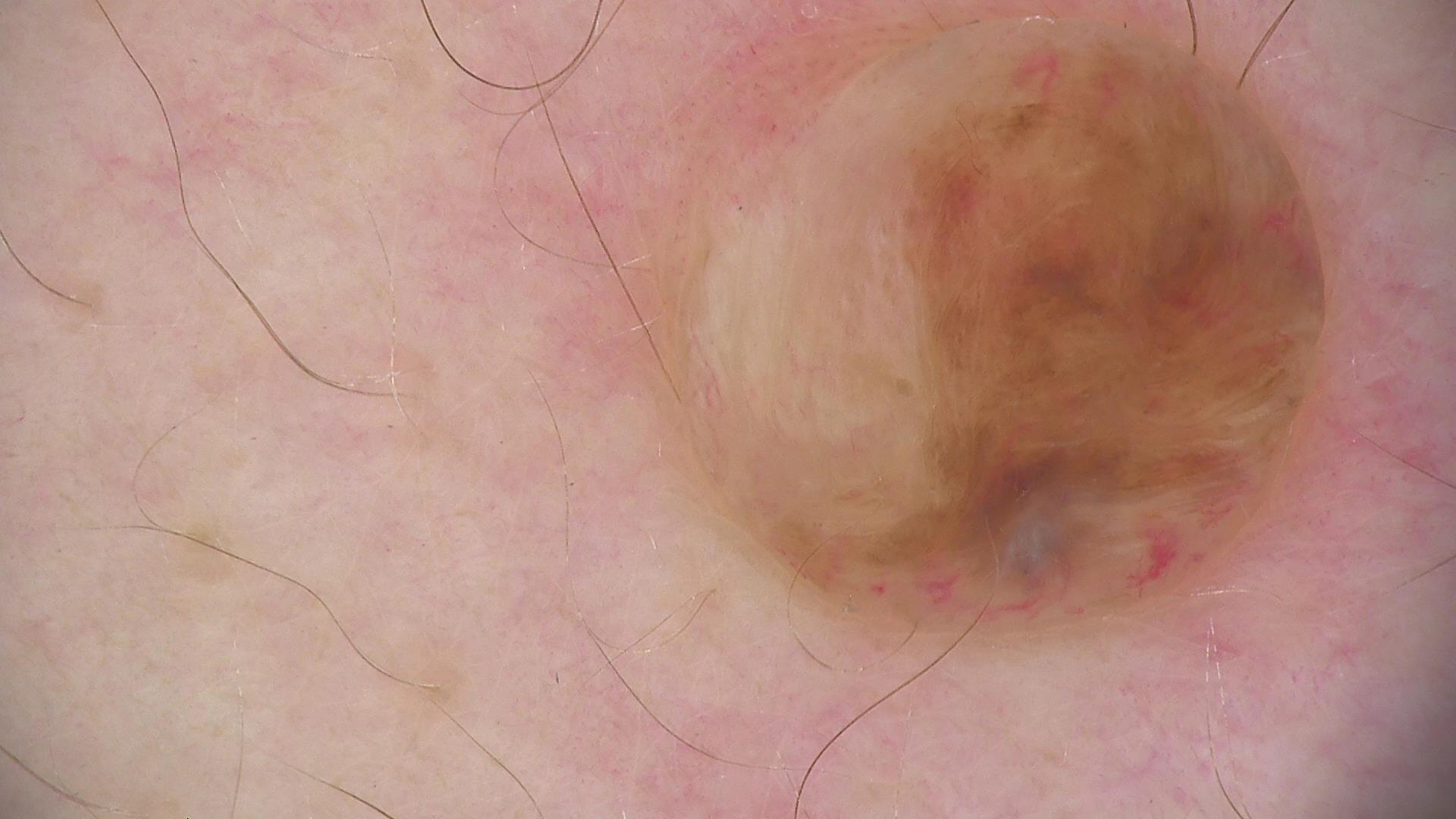A dermoscopic photograph of a skin lesion.
Diagnosed as a banal lesion — a dermal nevus.